Dermoscopy of a skin lesion, a male patient aged approximately 65.
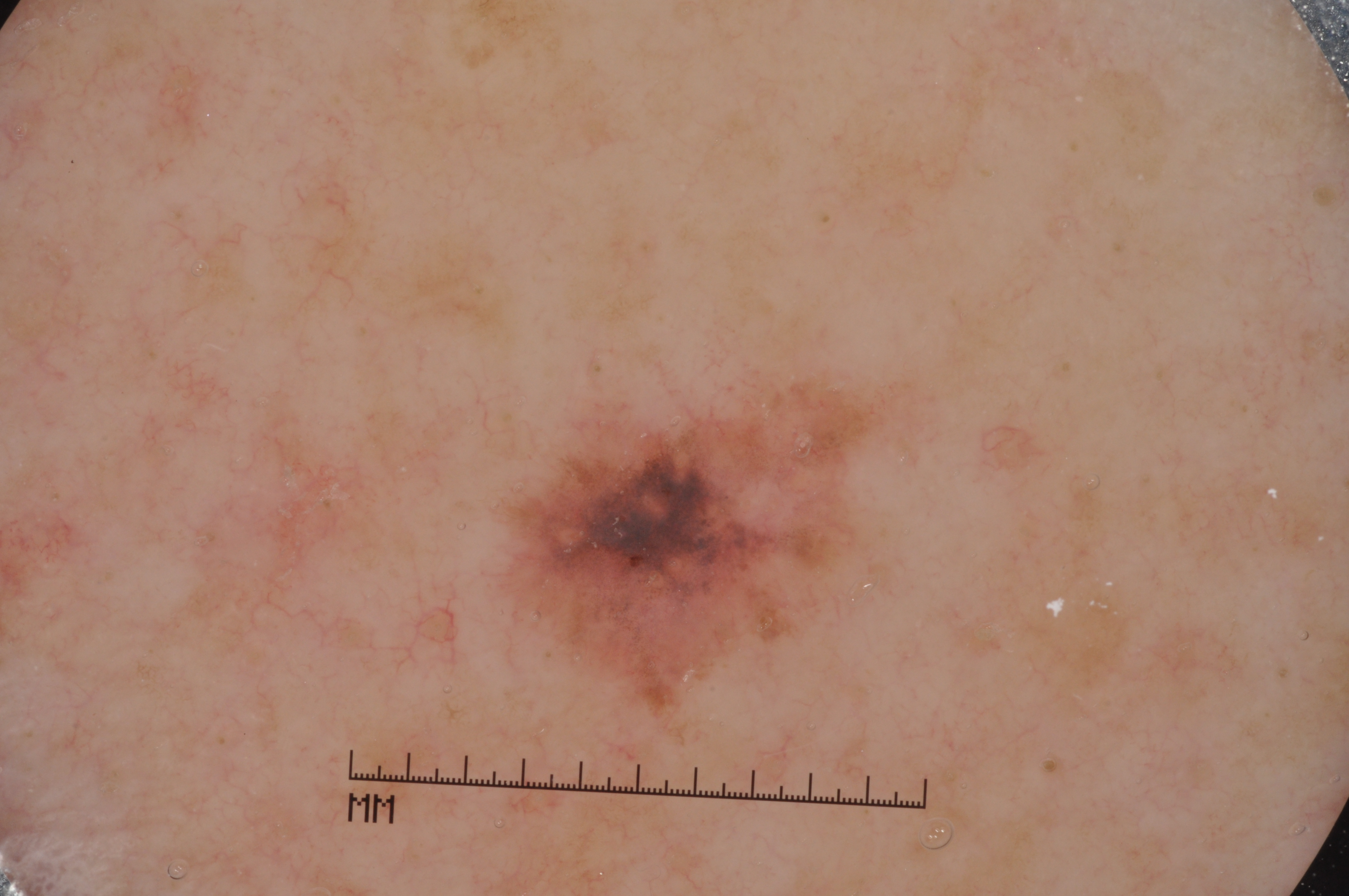Notes:
* lesion bbox — 517/385/875/693
* dermoscopic features assessed but absent — streaks, milia-like cysts, negative network, and pigment network
* diagnostic label — a melanoma